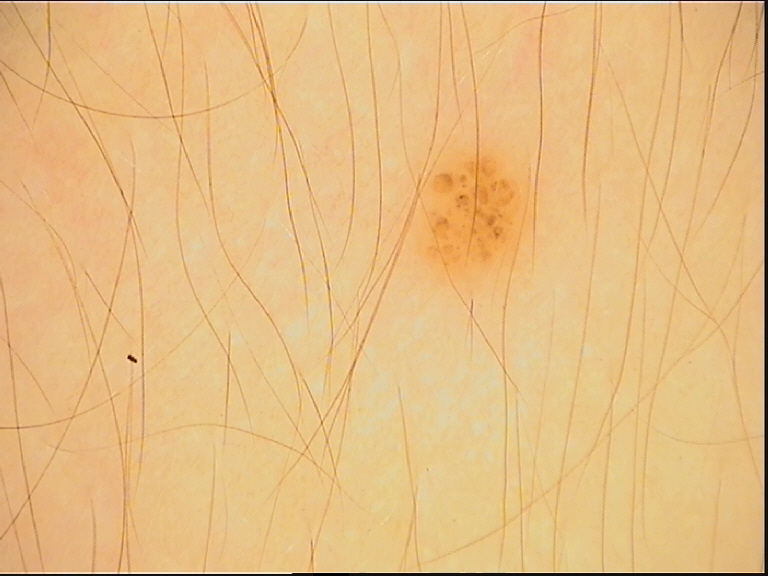Case:
• diagnostic label — junctional nevus (expert consensus)